Collected as part of a research study, without a referral diagnosis; on a questionnaire the patient reported a history of sunbed use; a female patient age 26; the patient describes having numerous moles; a clinical photograph showing a skin lesion: 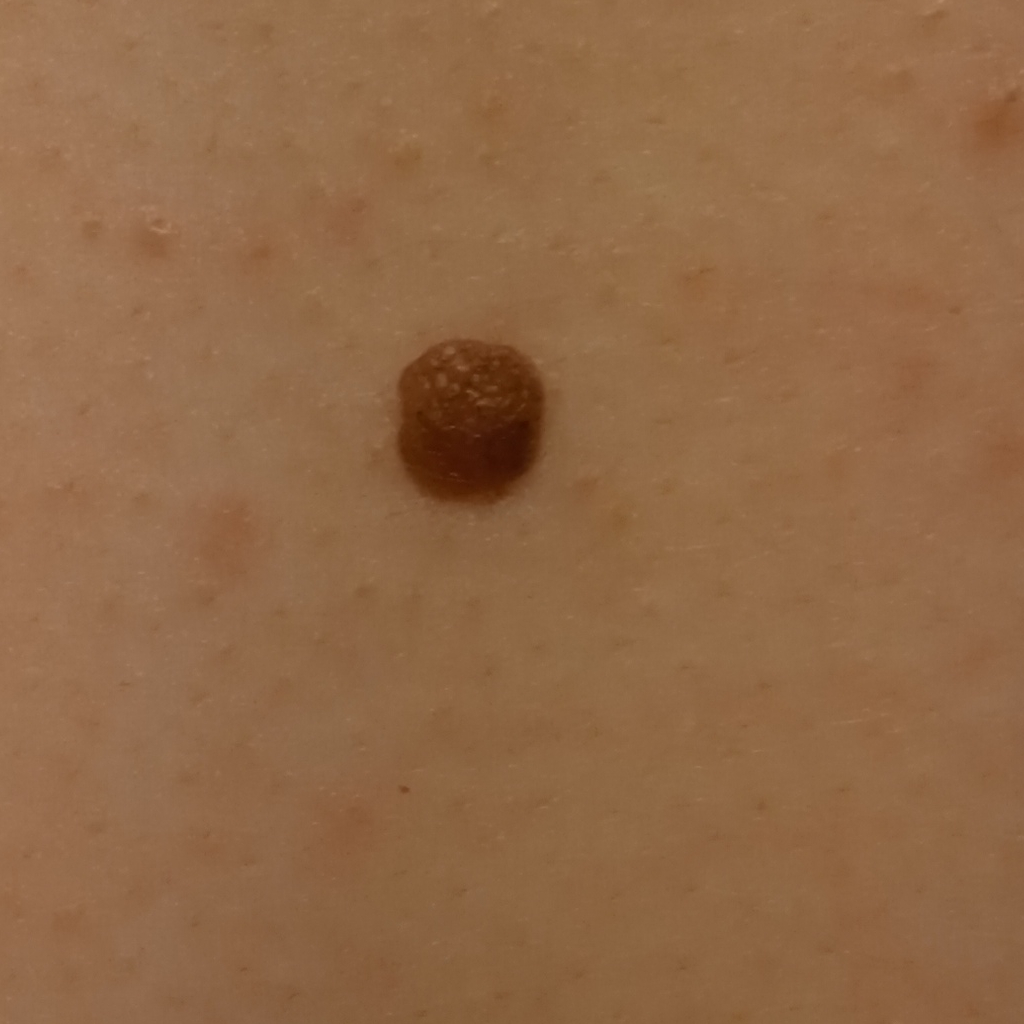lesion size=5.6 mm
diagnosis=melanocytic nevus (dermatologist consensus)